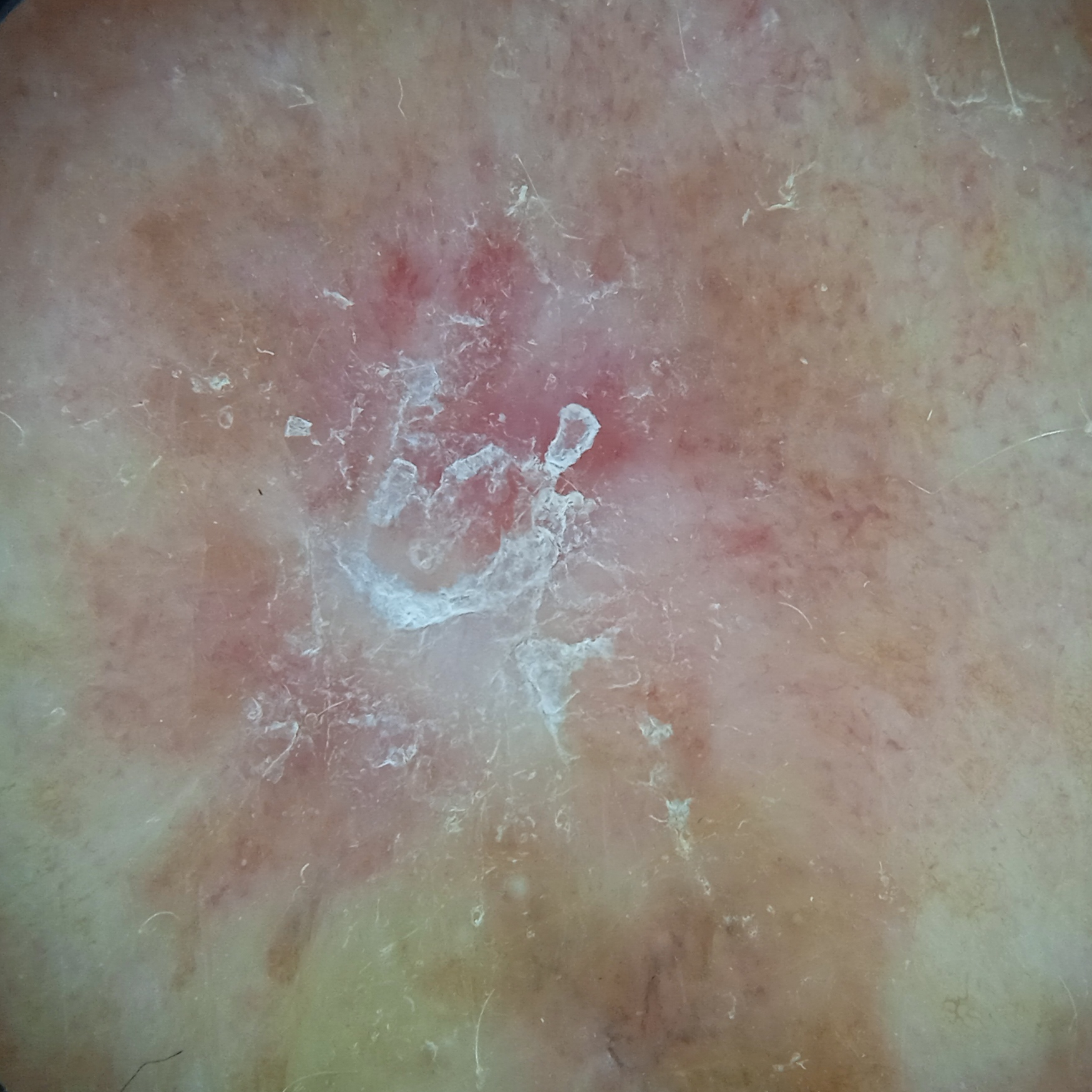By self-report, no prior organ transplant and no family history of skin cancer. A dermatoscopic image of a skin lesion. The patient describes having few moles overall. A male subject 62 years old. The lesion is about 13.8 mm across. Reviewed by four dermatologists, the consensus diagnosis was a squamous cell carcinoma; also considered: Bowen's disease.